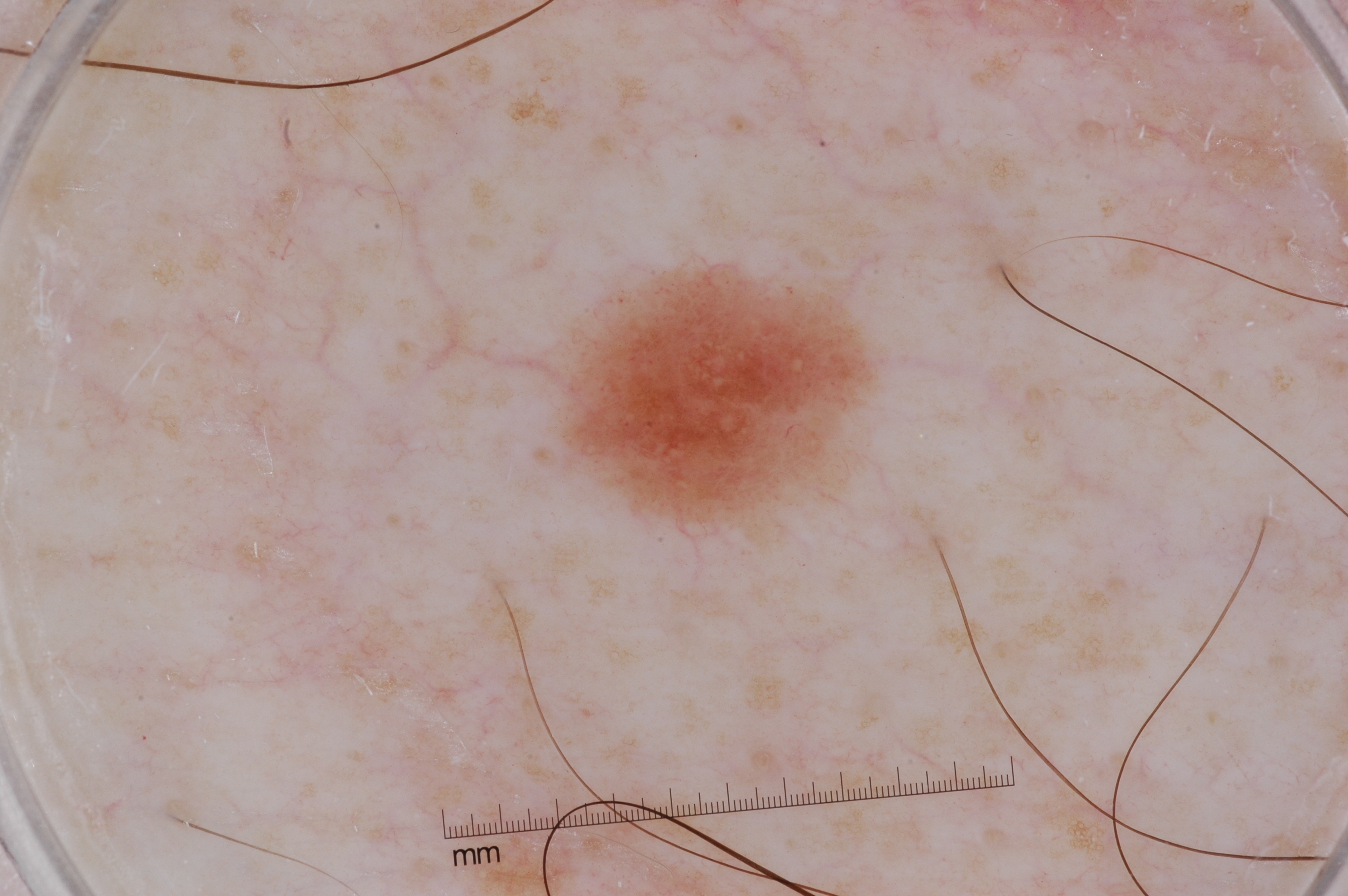A male patient aged approximately 50.
A dermoscopic close-up of a skin lesion.
Dermoscopy demonstrates no negative network, pigment network, streaks, or milia-like cysts.
The lesion is bounded by x1=569 y1=273 x2=874 y2=525.
Histopathological examination showed a melanoma, a skin cancer.